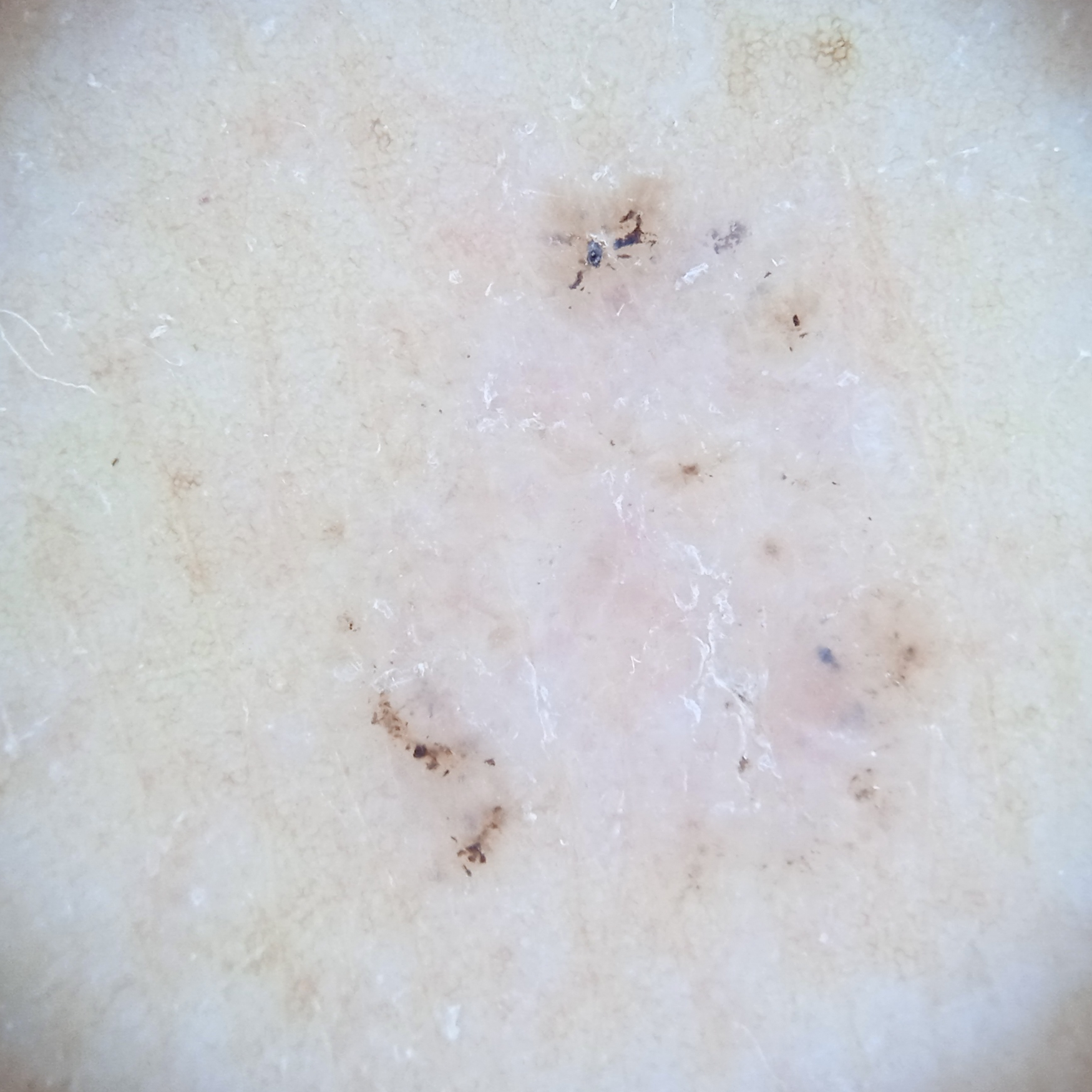subject = female, aged 60
imaging = dermoscopic image
nevus count = few melanocytic nevi overall
sun reaction = skin tans without first burning
referral context = clinical suspicion of basal cell carcinoma
relevant history = a personal history of cancer, a personal history of skin cancer
anatomic site = the back
diameter = 7.8 mm
assessment = basal cell carcinoma (dermatologist consensus)